A close-up photograph. The arm is involved:
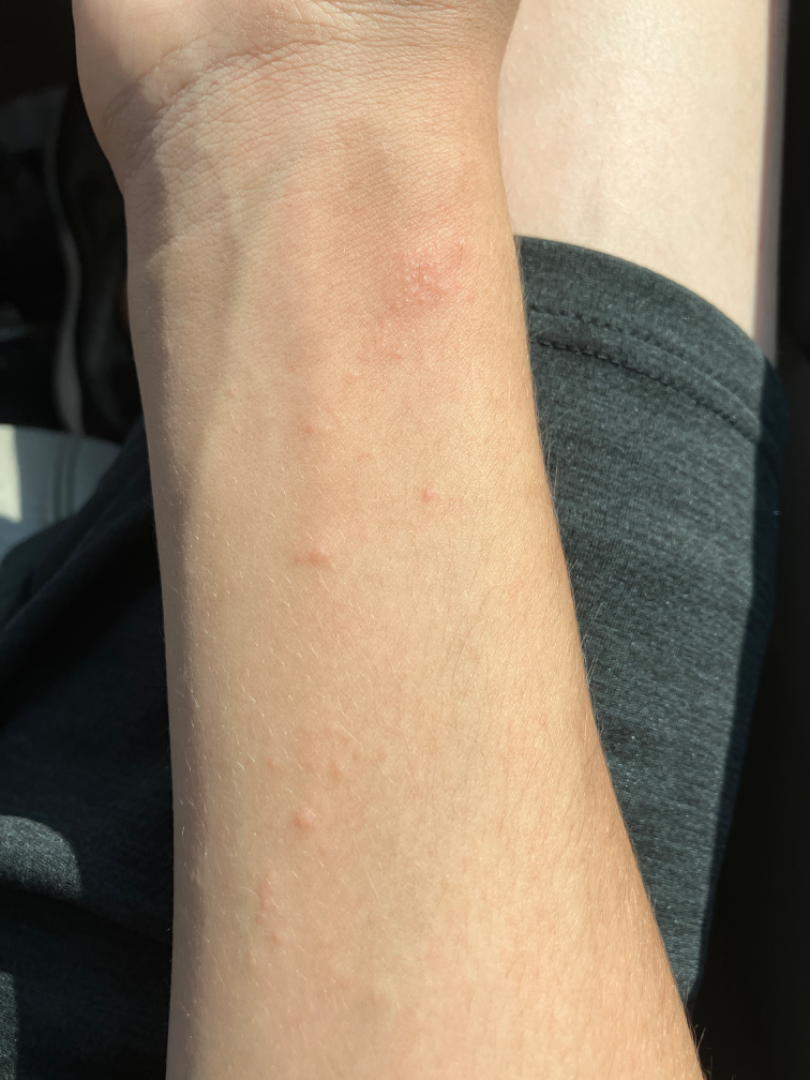The condition has been present for about one day.
Texture is reported as raised or bumpy.
The patient considered this a rash.
The lesion is associated with itching.
On dermatologist assessment of the image, most consistent with Allergic Contact Dermatitis; possibly Eczema; lower on the differential is Insect Bite.